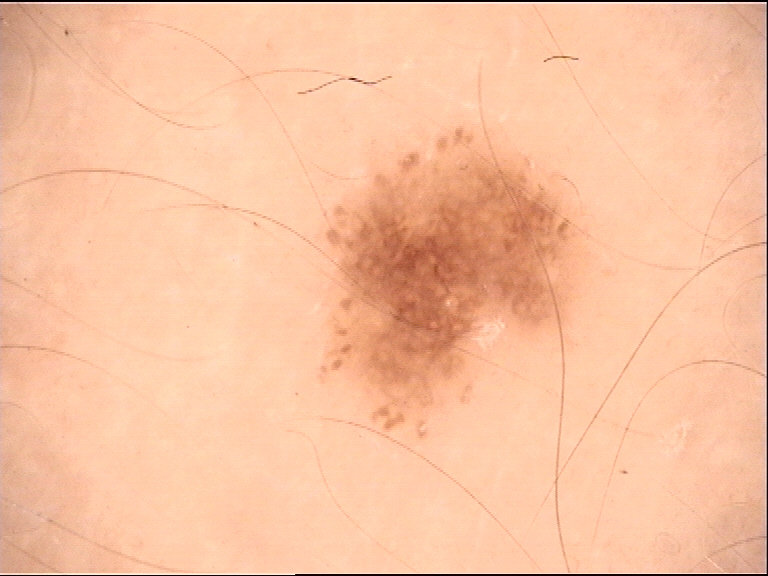Conclusion: The diagnostic label was a dysplastic junctional nevus.